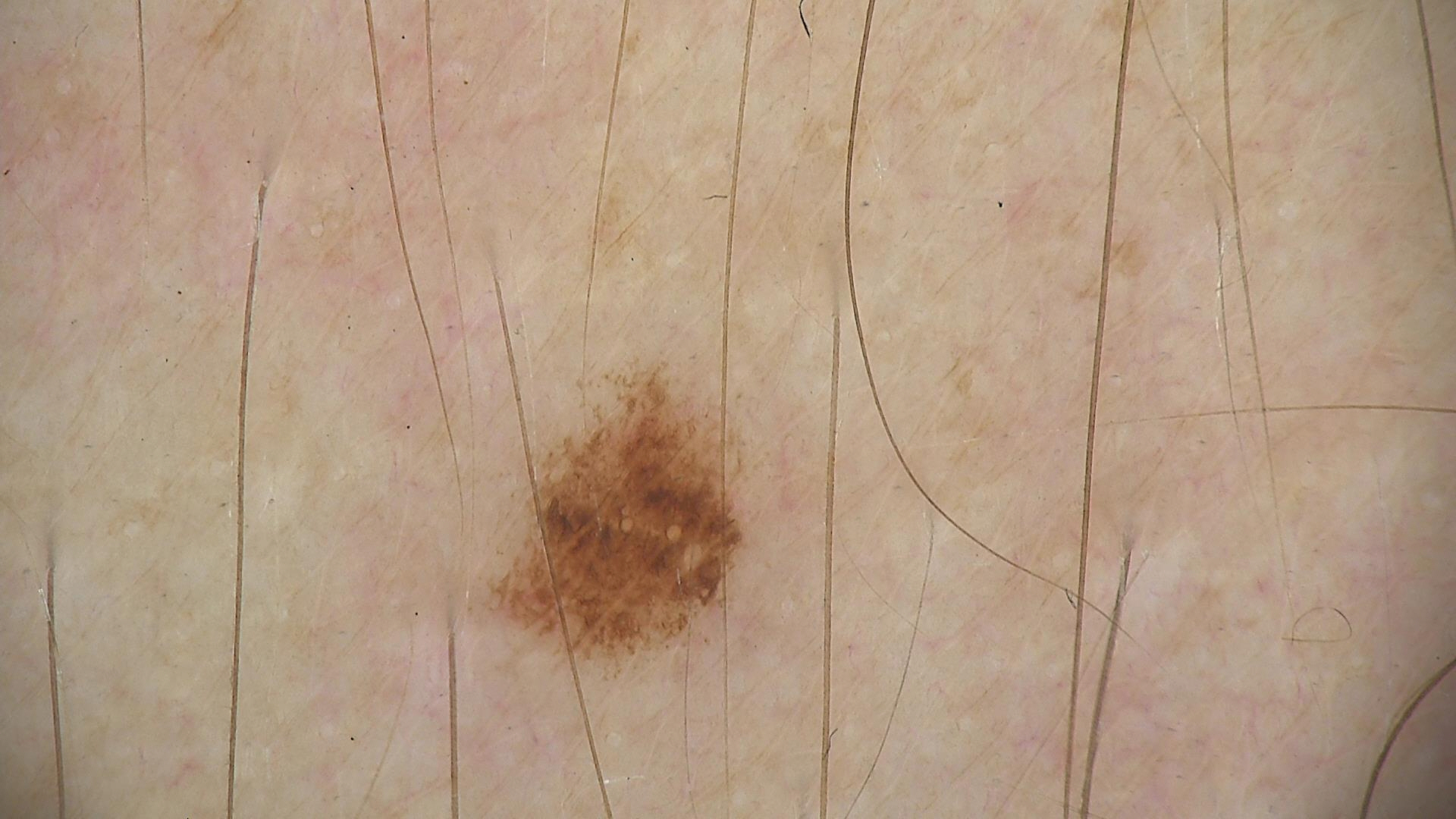assessment: dysplastic junctional nevus (expert consensus).